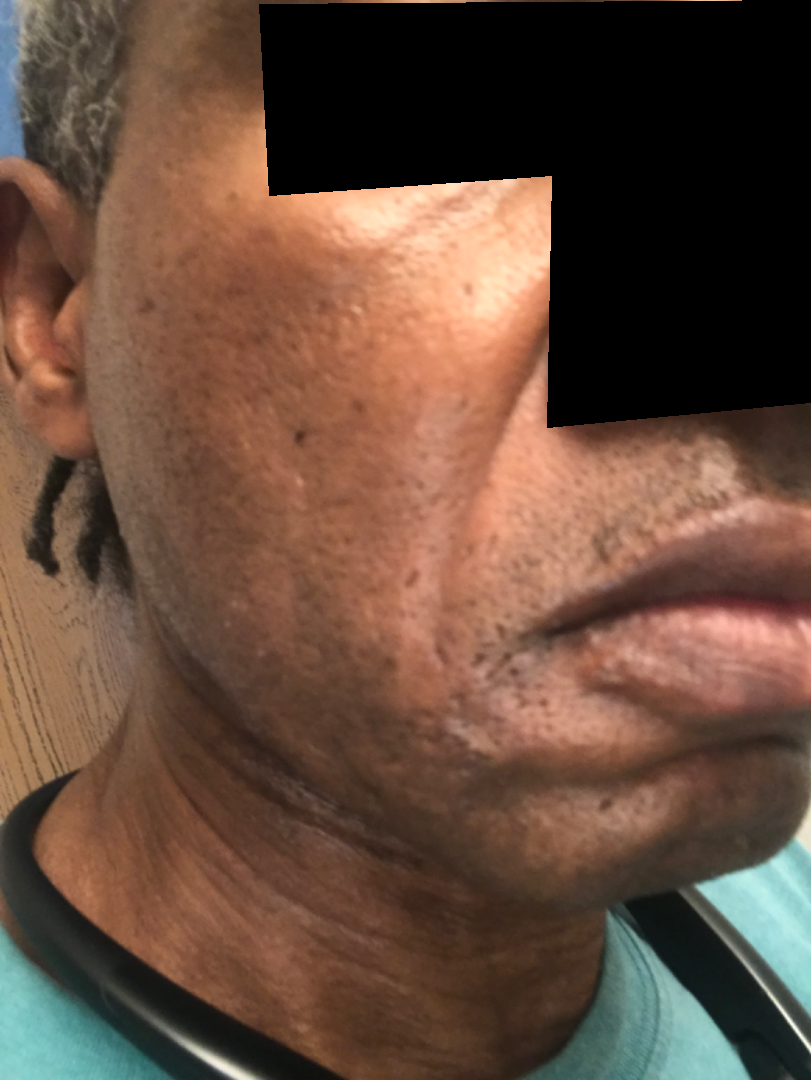image framing: at an angle | subject: male | location: head or neck | self-categorized as: skin that appeared healthy to them | duration: one to four weeks | skin tone: Fitzpatrick skin type V; lay graders estimated Monk Skin Tone 5 or 7 (two reviewer pools disagreed) | surface texture: raised or bumpy | symptoms: itching | diagnostic considerations: Post-Inflammatory hyperpigmentation and Scar Condition were each considered, in no particular order.